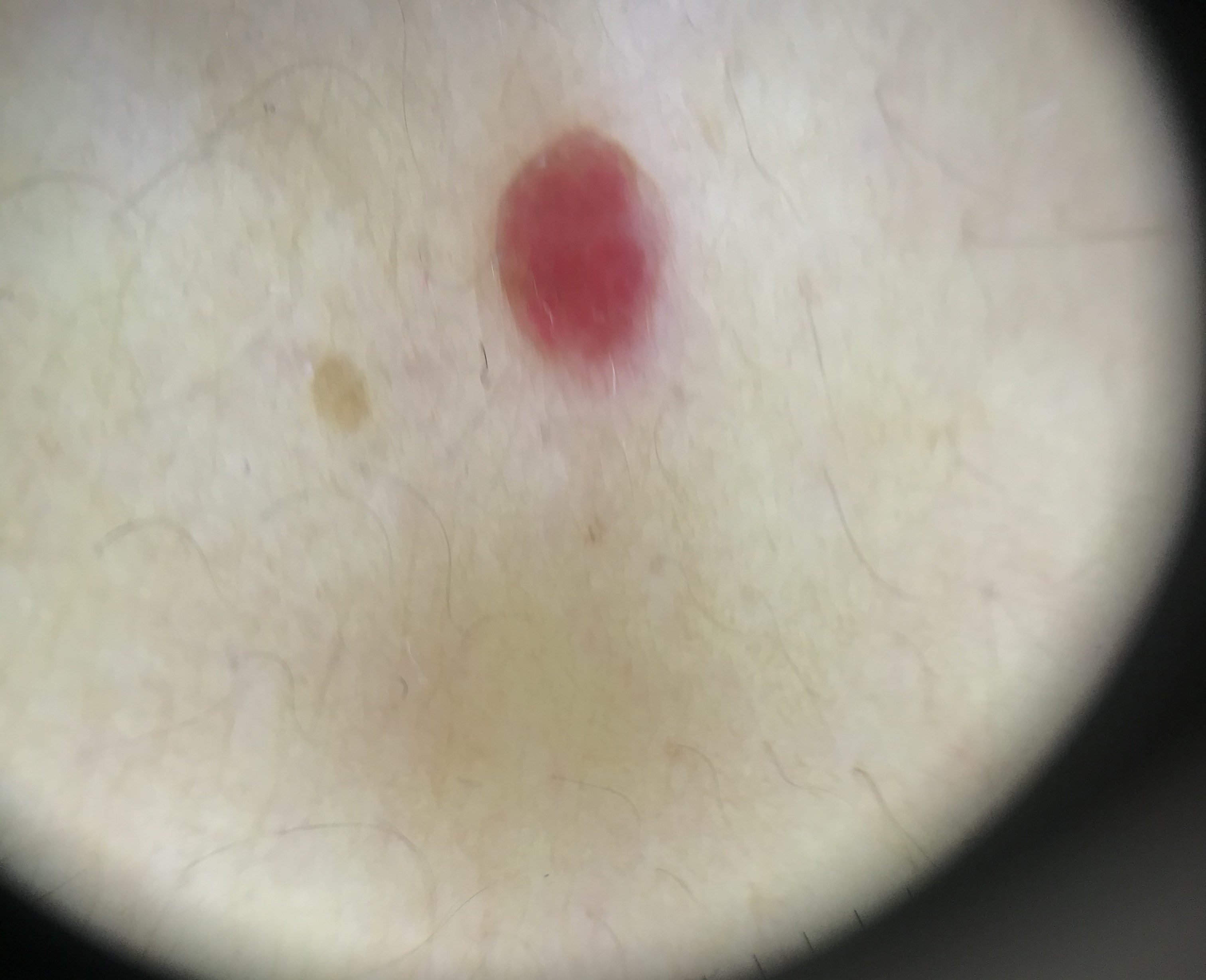A dermatoscopic image of a skin lesion. Classified as a hemangioma.